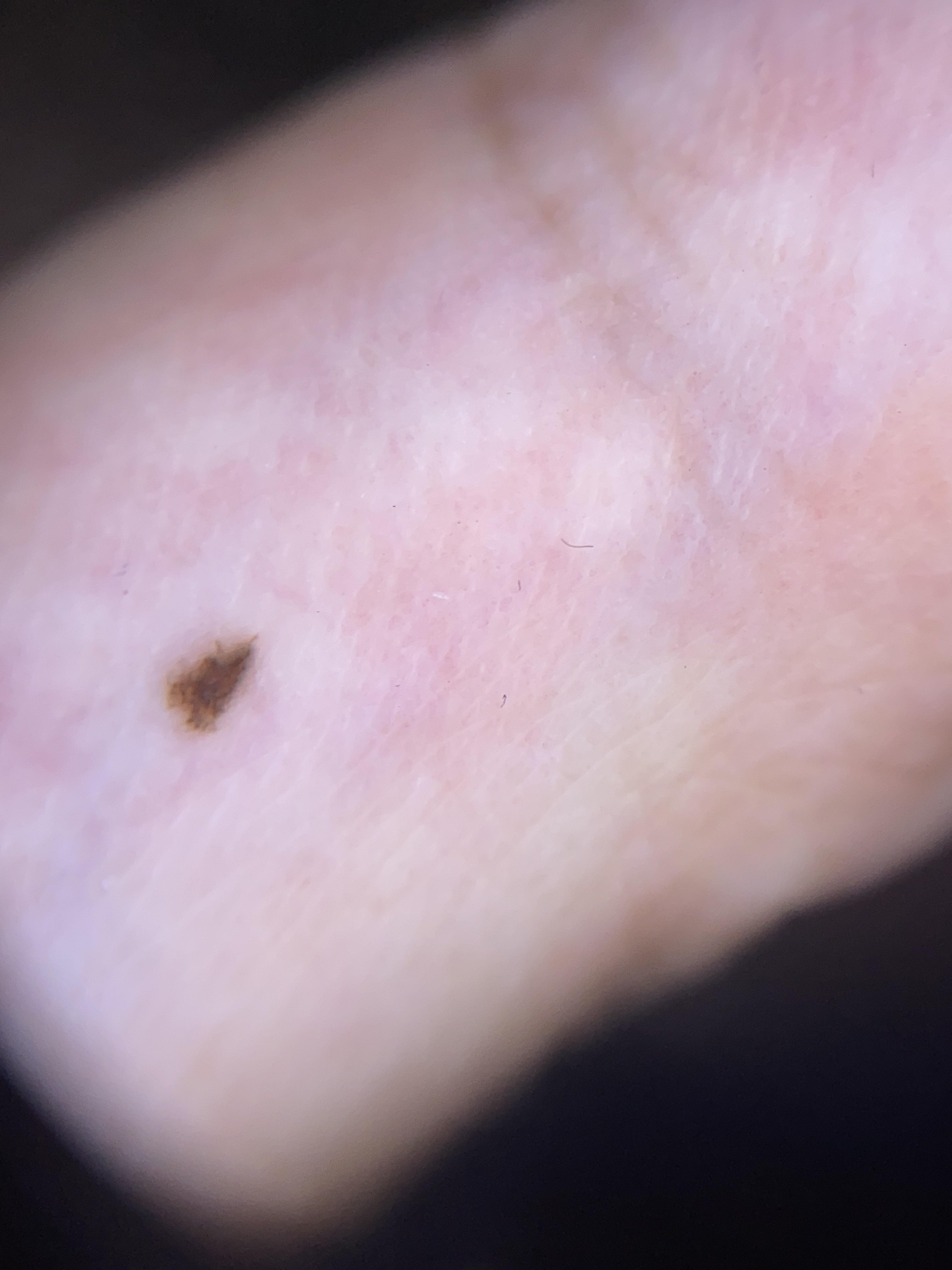The diagnostic impression was a nevus.